The patient was assessed as FST I. A dermatoscopic image of a skin lesion. A female patient in their 70s.
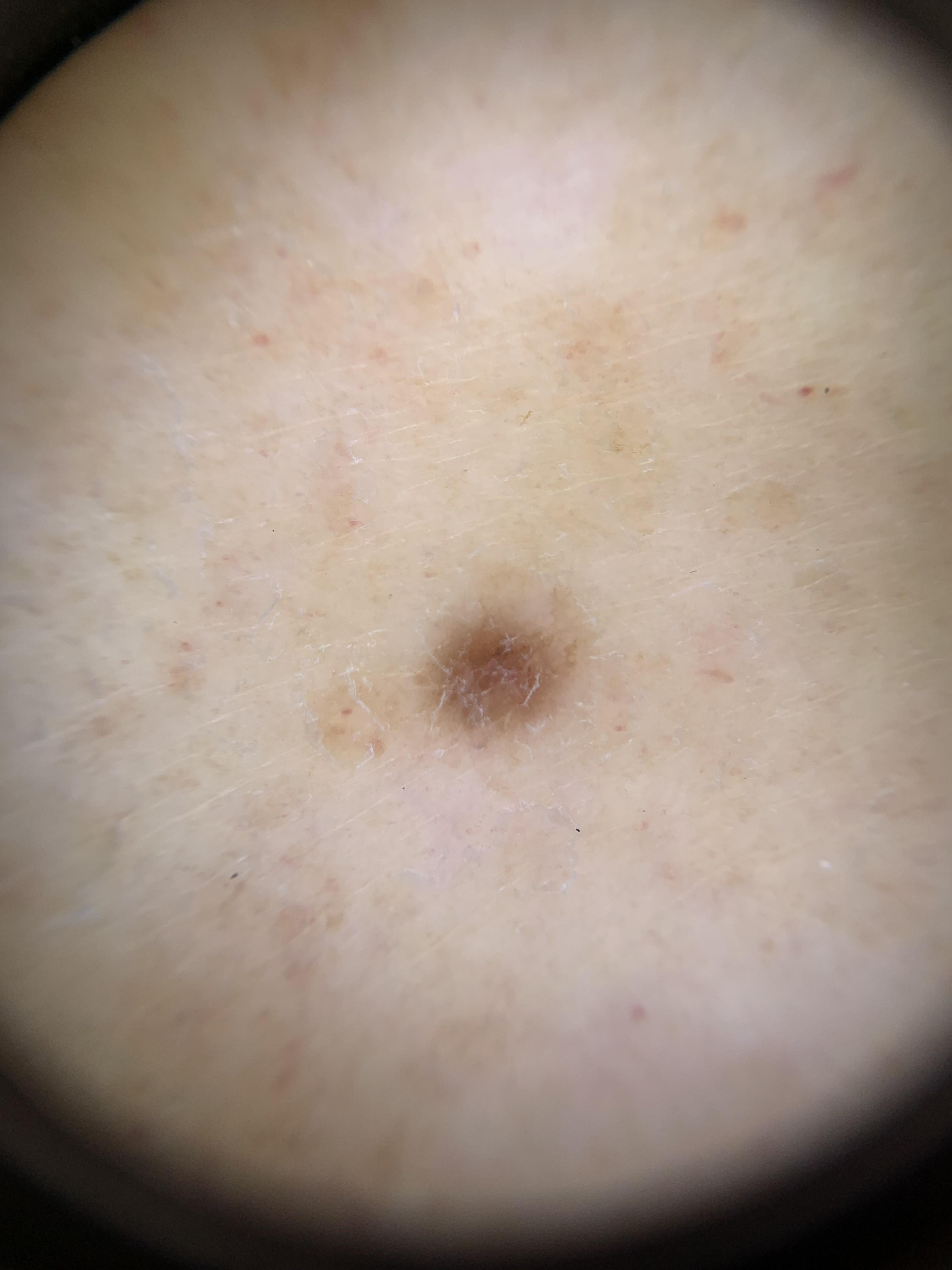- site — a lower extremity
- diagnosis — Dermatofibroma (clinical impression)